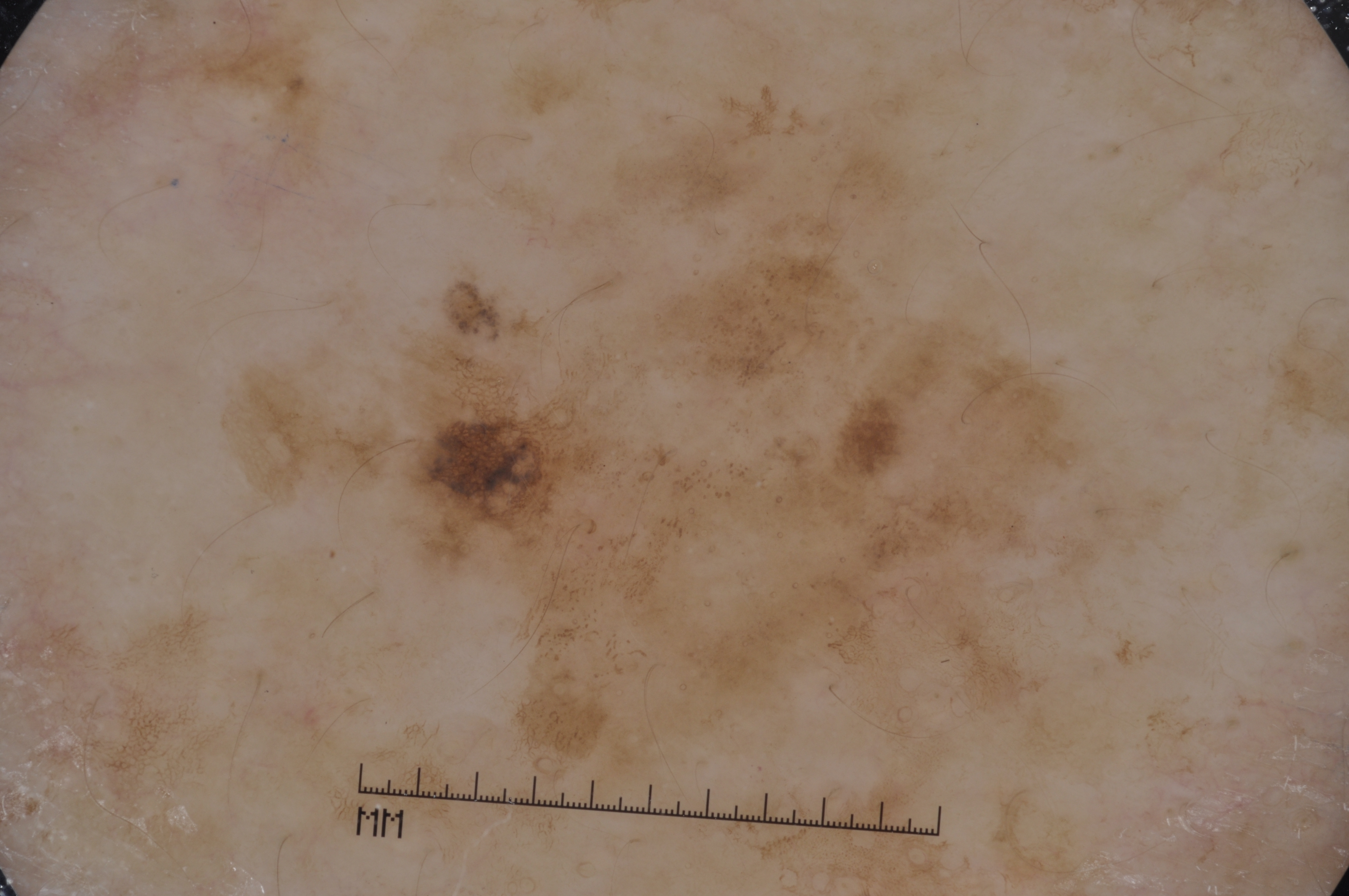image:
  modality: dermoscopy
patient:
  sex: male
  age_approx: 80
dermoscopic_features:
  present:
    - pigment network
    - milia-like cysts
  absent:
    - negative network
    - streaks
lesion_extent:
  approx_field_fraction_pct: 39
lesion_location:
  bbox_xyxy:
    - 219
    - 80
    - 1172
    - 805
diagnosis:
  name: melanocytic nevus
  malignancy: benign
  lineage: melanocytic
  provenance: clinical